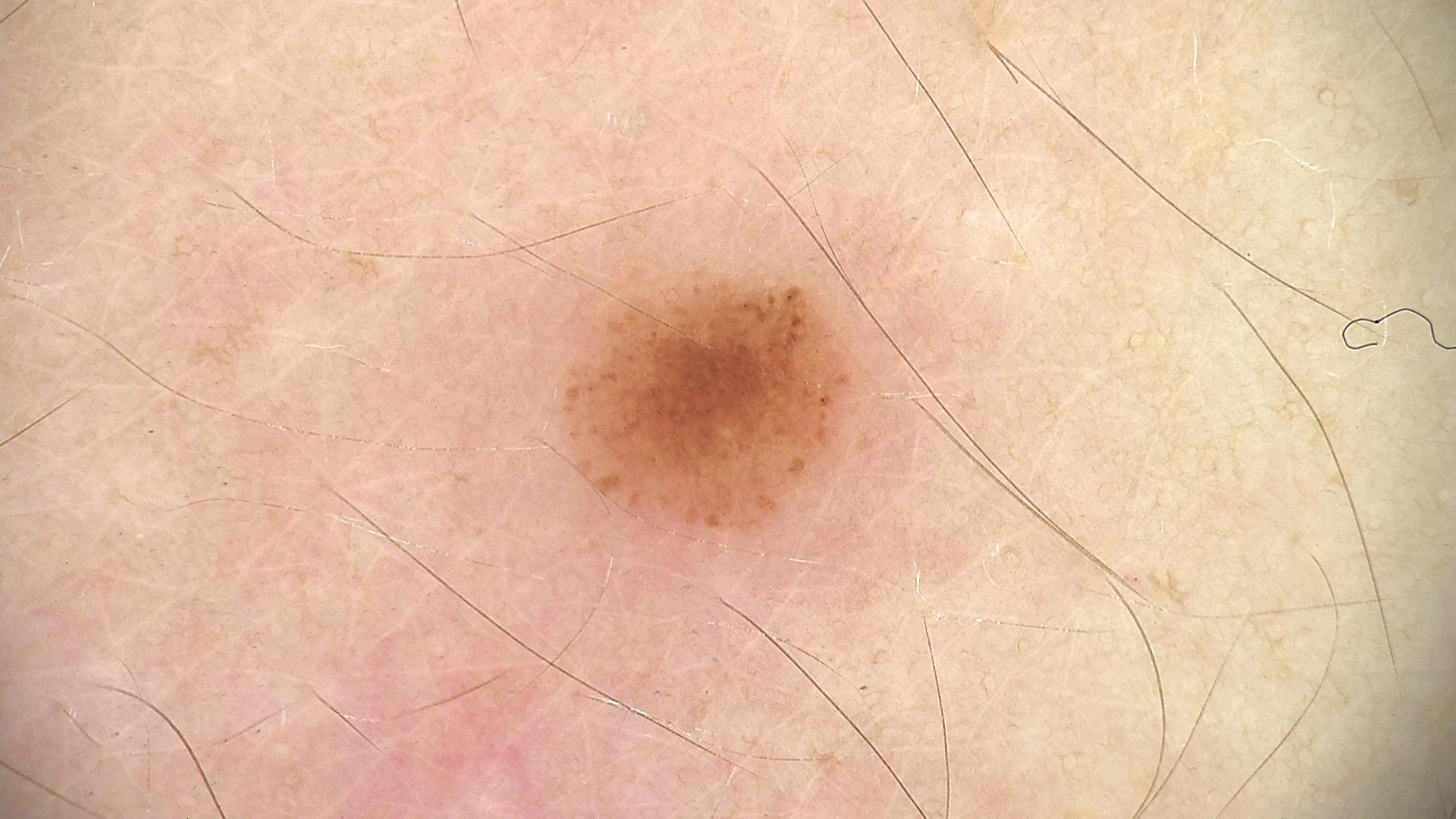image type=dermatoscopy
label=dysplastic junctional nevus (expert consensus)